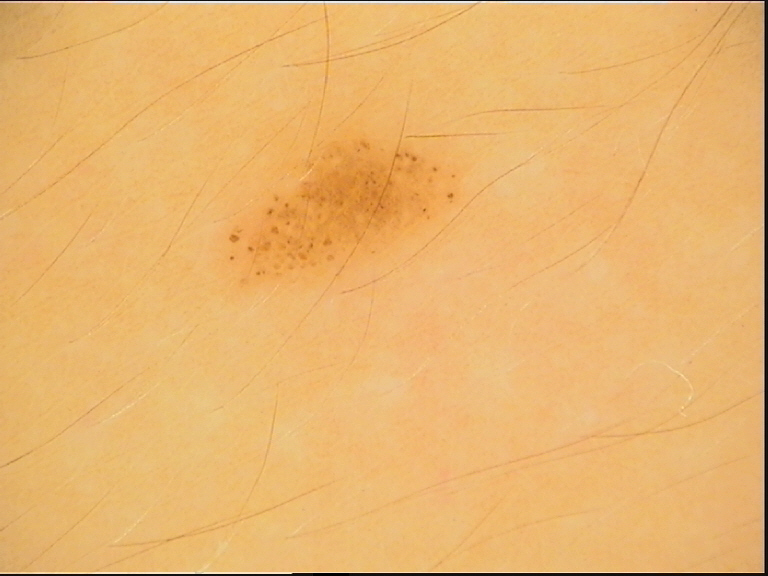imaging — dermoscopy | label — junctional nevus (expert consensus).